This image was taken at a distance; the leg is involved; female contributor, age 40–49:
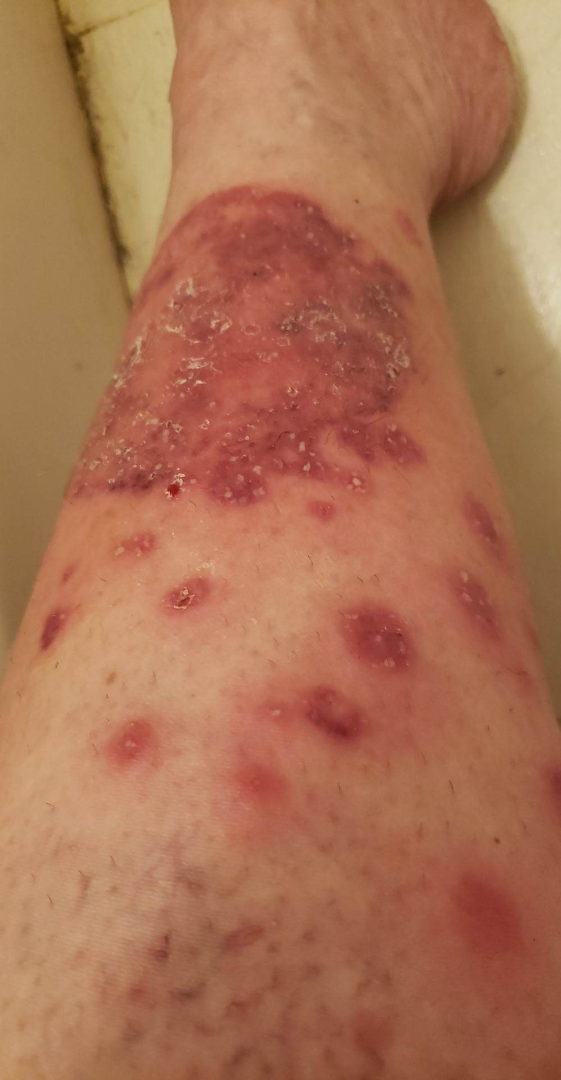  differential:
    - Psoriasis
    - Deep fungal infection
    - Eczema